Located on the front of the torso, arm, leg, head or neck and back of the torso. The contributor is female. The lesion is described as fluid-filled and raised or bumpy. Reported duration is less than one week. This image was taken at a distance. The patient considered this a rash.
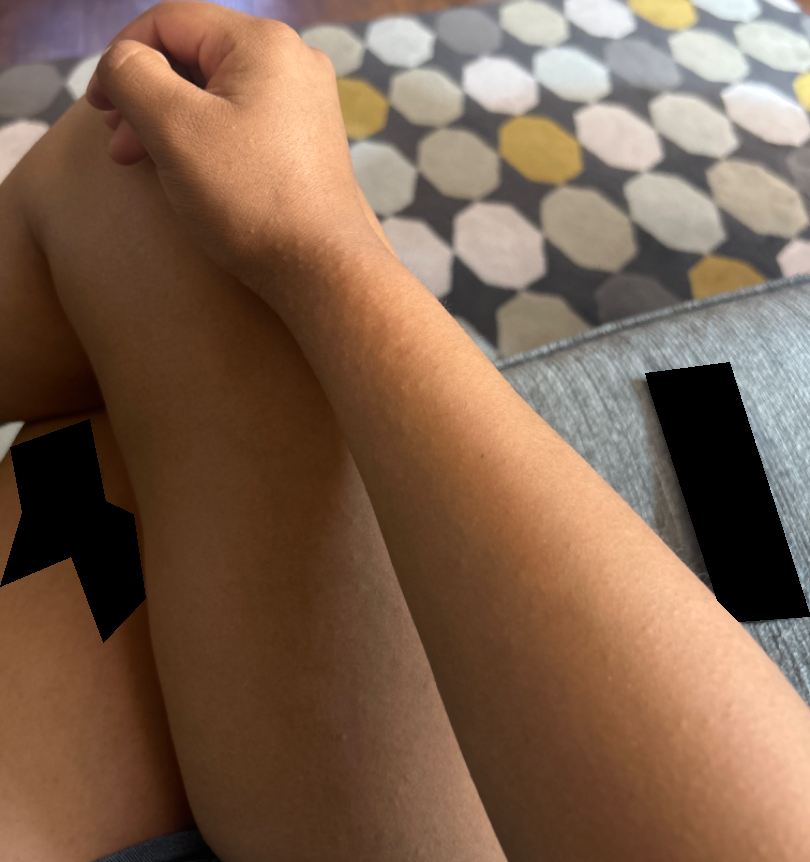Assessment:
Three dermatologists each reviewed the case: favoring Allergic Contact Dermatitis; an alternative is Acute dermatitis, NOS; a more distant consideration is Miliaria; less likely is Hypersensitivity; lower on the differential is Eczema.